A close-up photograph:
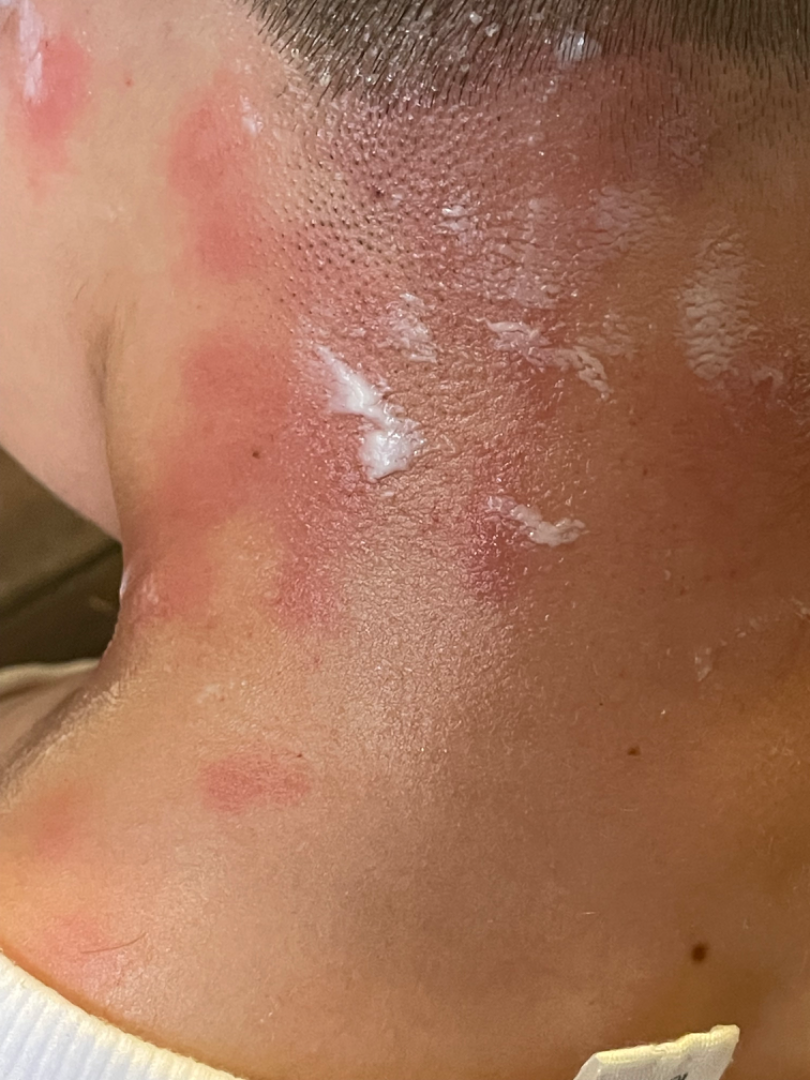<case>
<differential>
  <tied_lead>Insect Bite, Allergic Contact Dermatitis</tied_lead>
  <unlikely>Urticaria</unlikely>
</differential>
</case>